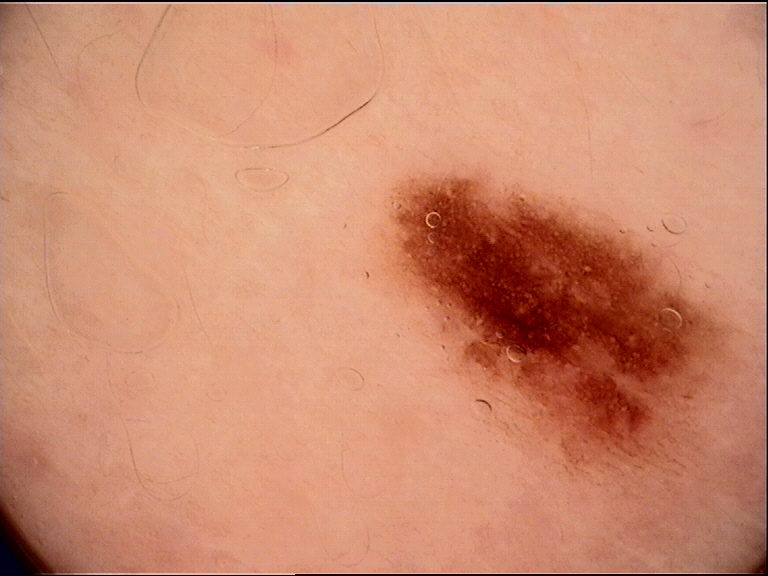Case:
• image type · dermatoscopy
• class · dysplastic junctional nevus (expert consensus)